The photo was captured at an angle. The subject is 50–59, female. The leg is involved:
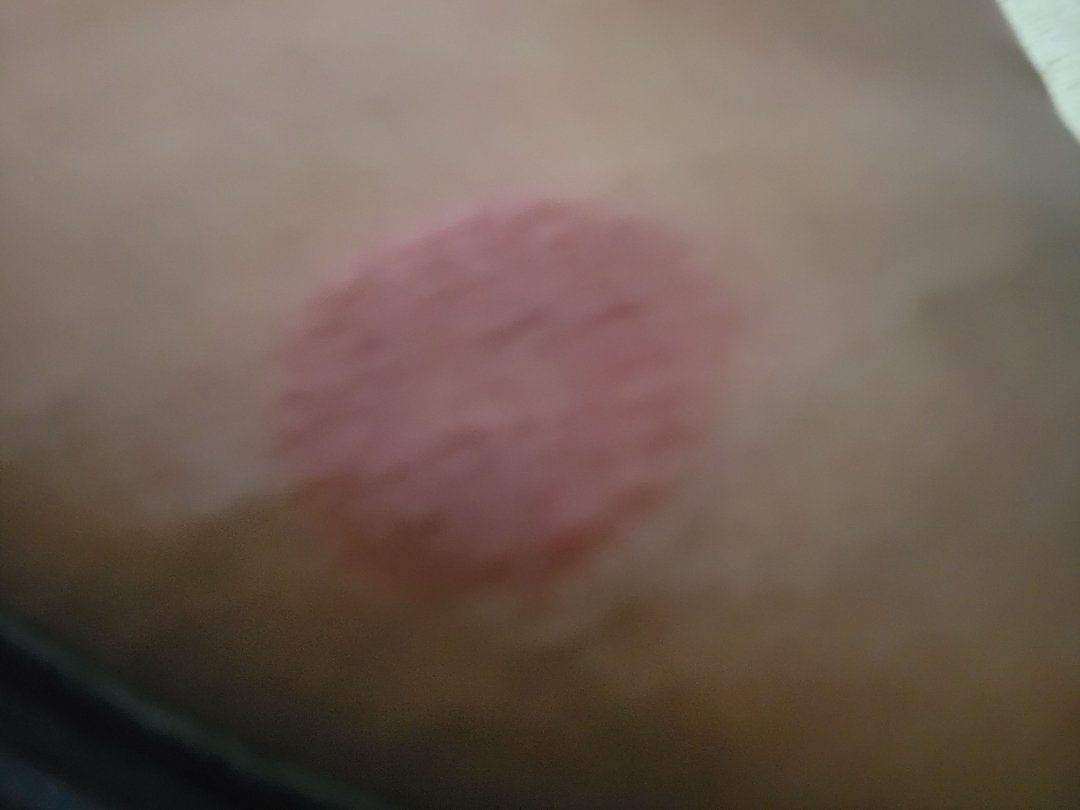The reviewing dermatologist's impression was: Psoriasis and Cutaneous T Cell Lymphoma were considered with similar weight.